A male subject 63 years of age:
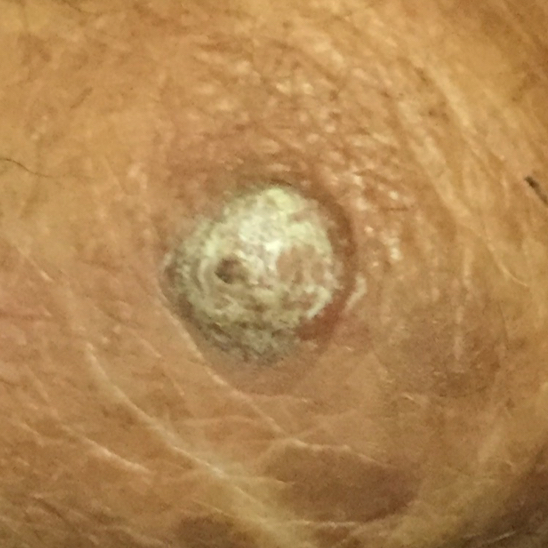Findings:
- region — an arm
- symptoms — growth, elevation / no pain
- pathology — actinic keratosis (biopsy-proven)